The patient says their skin reddens with sun exposure; a male subject 62 years of age; the patient reports no family history of skin cancer; acquired for a research image collection, with no referral diagnosis:
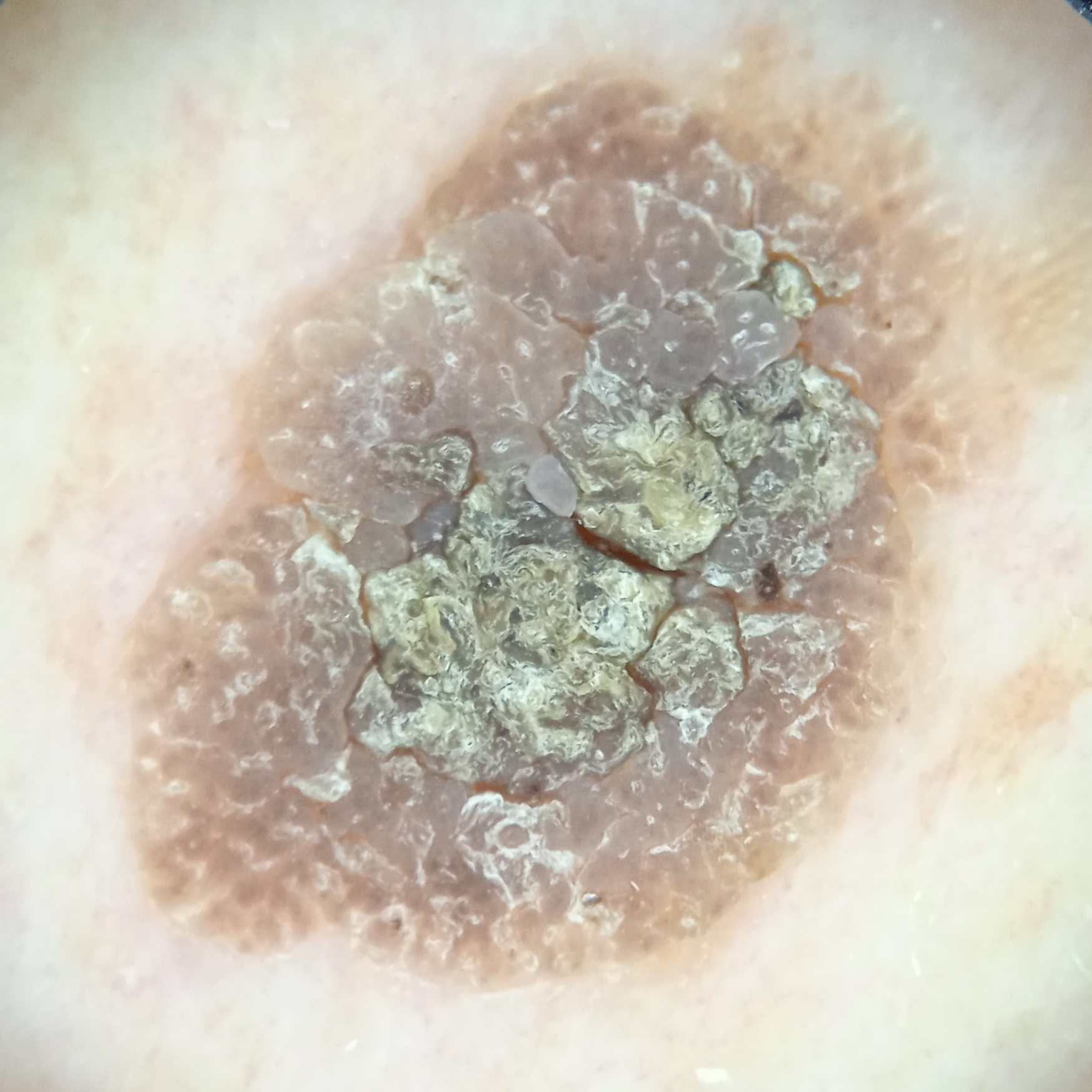The lesion is on the back.
The lesion measures approximately 10.9 mm.
The dermatologists' assessment was a seborrheic keratosis.